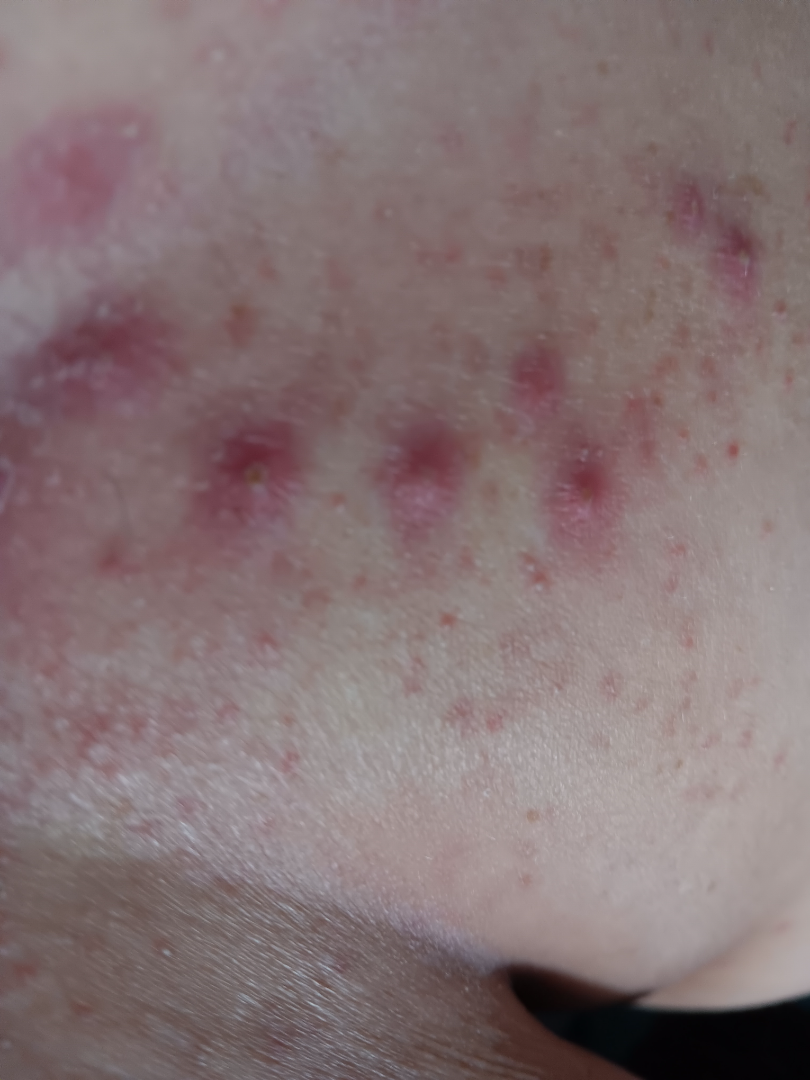image framing=close-up
affected area=front of the torso
subject=female, age 50–59
differential diagnosis=Folliculitis (considered); Insect Bite (considered); Localized skin infection (lower probability)